A female subject 67 years of age; the patient says their skin reddens with sun exposure; imaged for a research study, with no referral diagnosis recorded; a dermatoscopic image of a skin lesion:
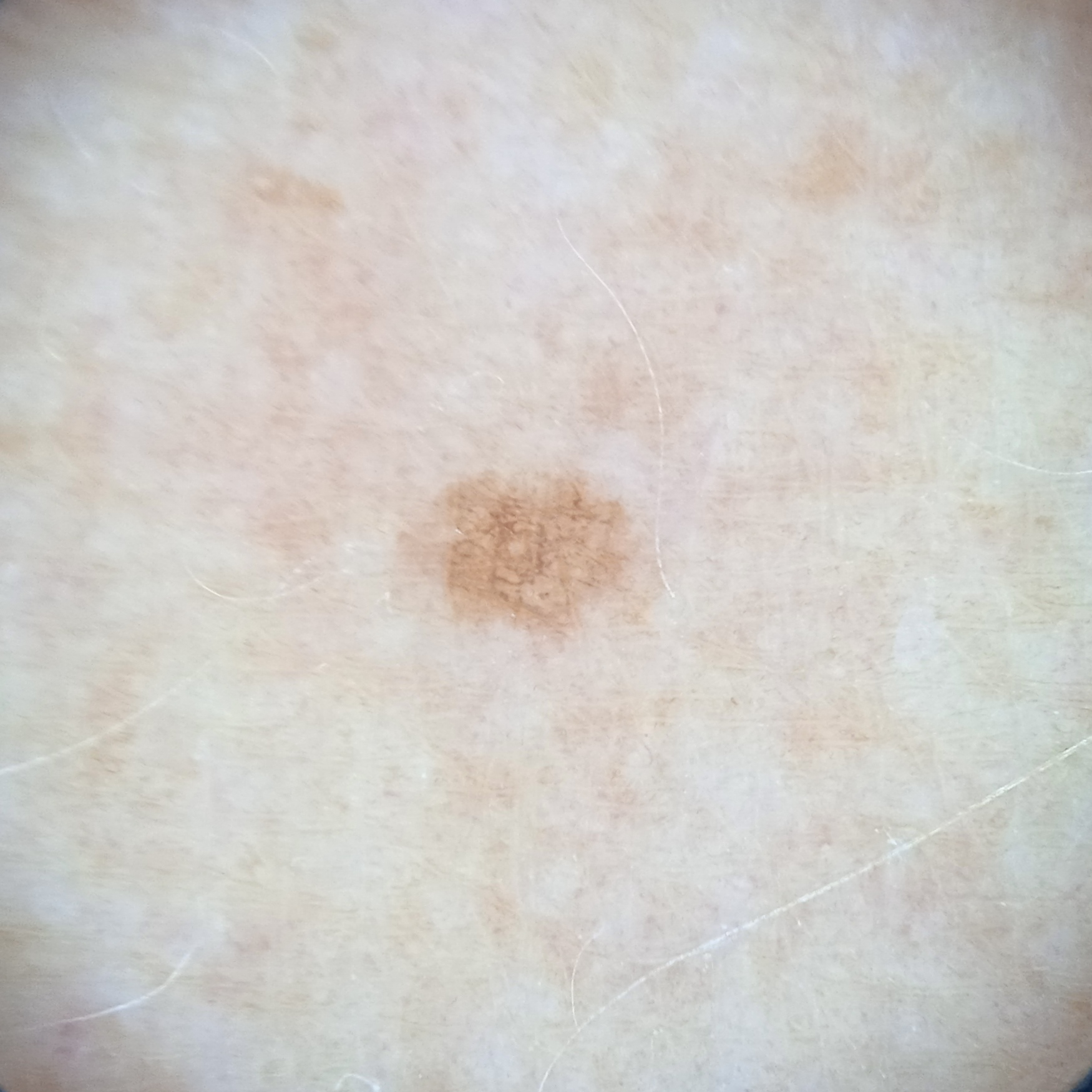lesion_location: an arm
lesion_size:
  diameter_mm: 2.3
diagnosis:
  name: melanocytic nevus
  malignancy: benign